A dermoscopic close-up of a skin lesion.
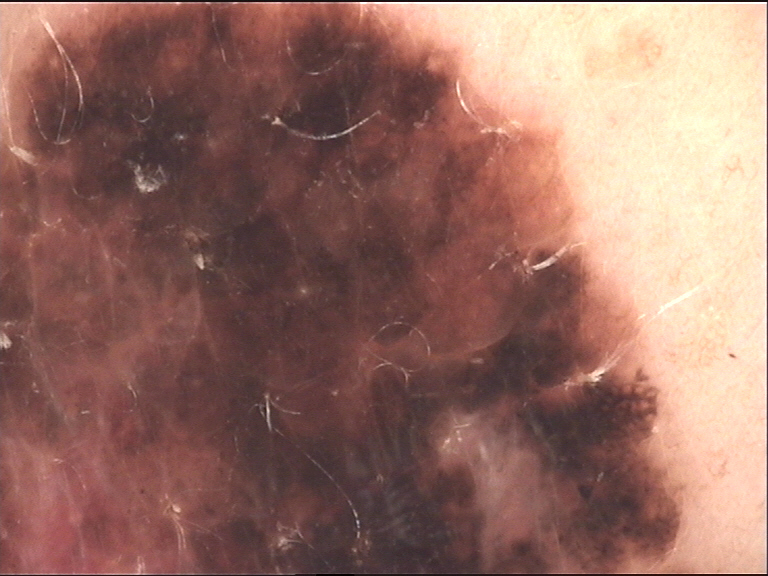Confirmed on histopathology as a melanoma.